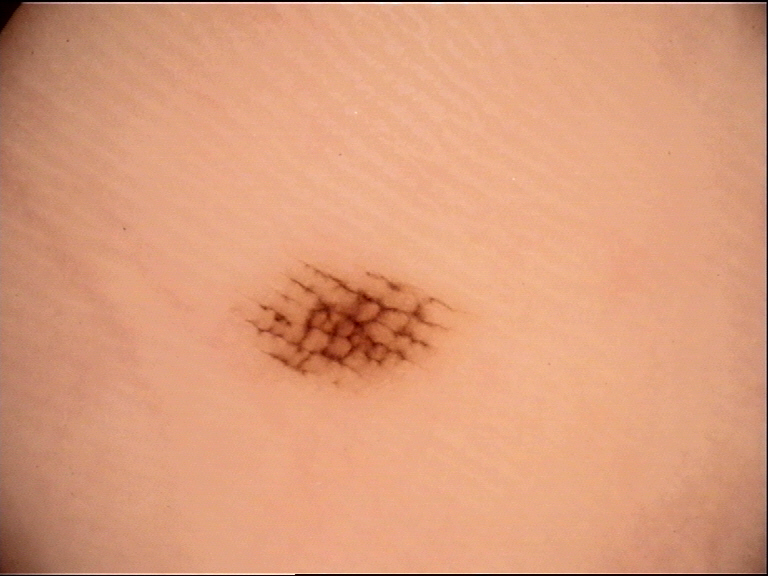image=dermatoscopy
diagnostic label=acral dysplastic junctional nevus (expert consensus)